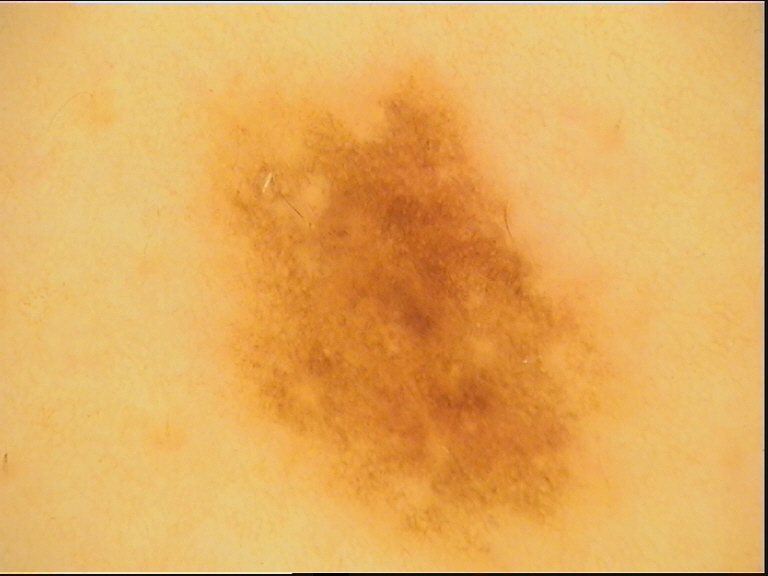Conclusion: Classified as a dysplastic junctional nevus.